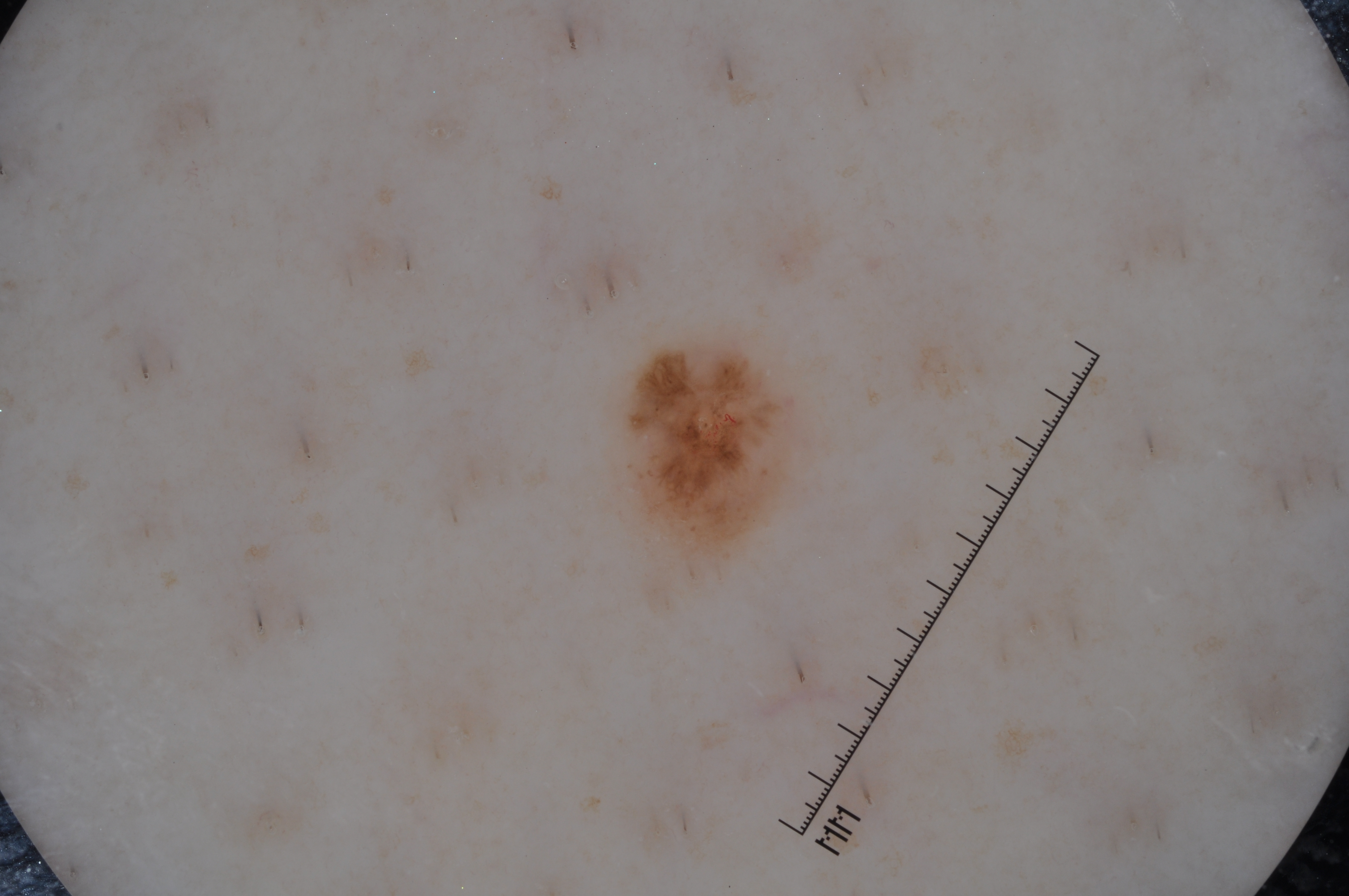imaging — dermatoscopic image of a skin lesion; patient — female, aged 33 to 37; dermoscopic pattern — milia-like cysts and pigment network; lesion bbox — 622/343/790/553; impression — a melanocytic nevus.